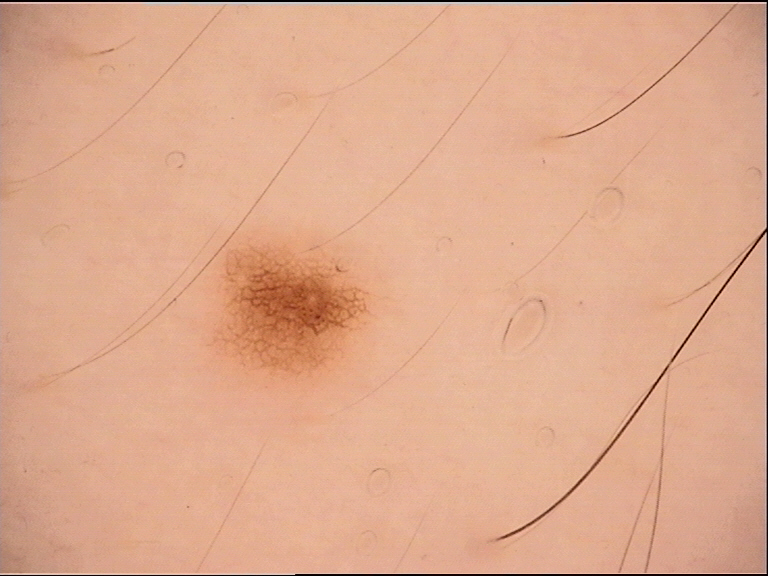Conclusion: Consistent with a dysplastic junctional nevus.